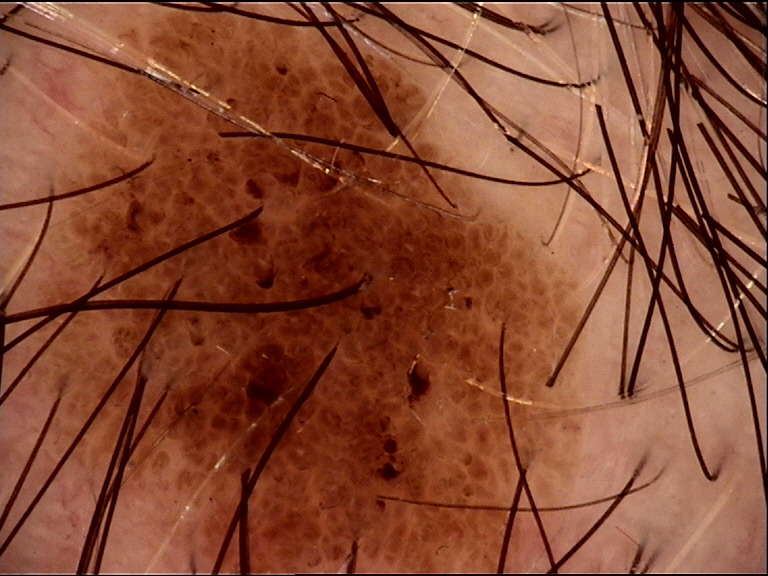imaging — dermoscopy
label — compound nevus (expert consensus)